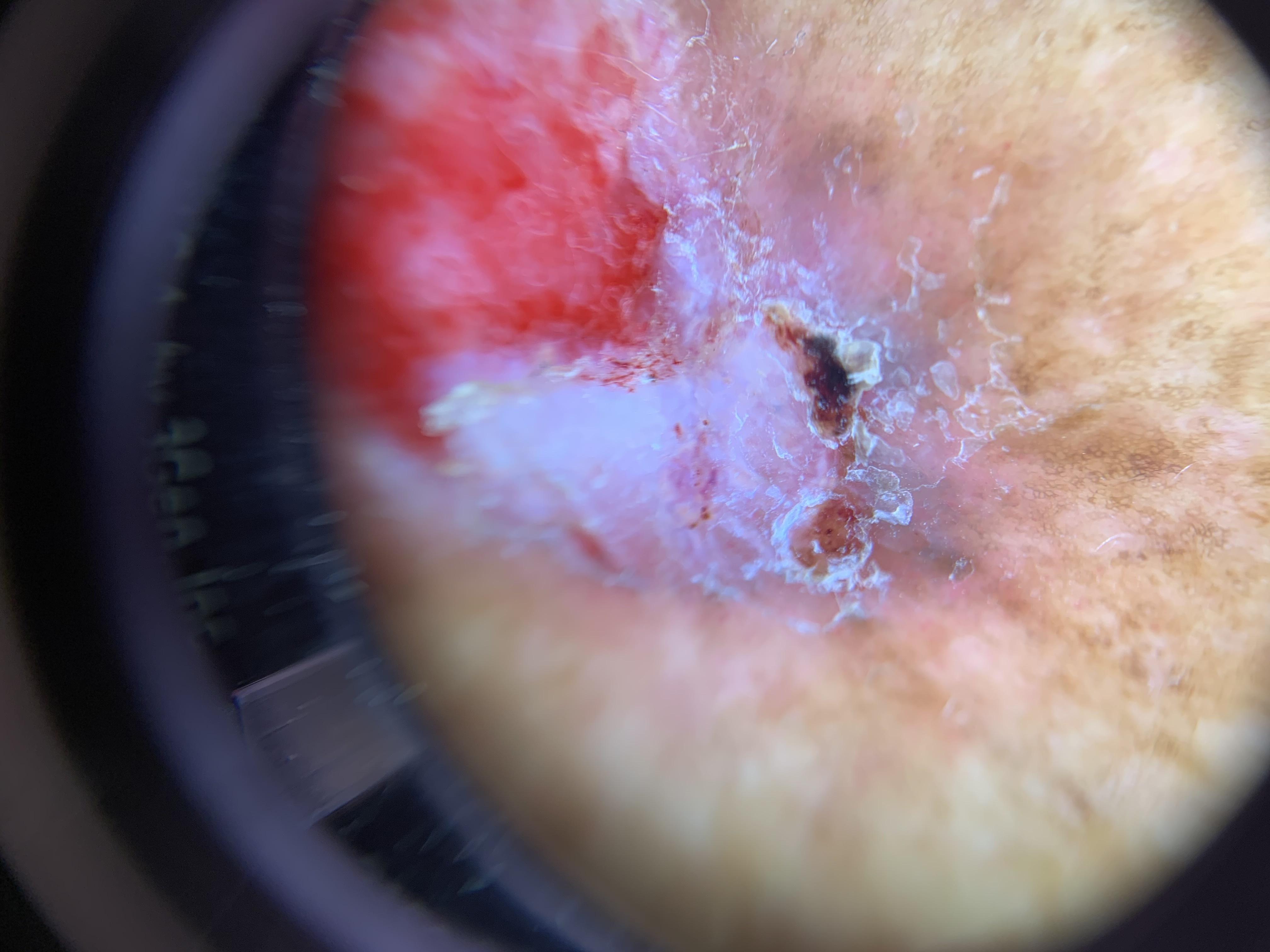A male patient aged approximately 75. The patient was assessed as Fitzpatrick II. Located on a lower extremity. Histopathology confirmed a basal cell carcinoma.